A dermoscopic photograph of a skin lesion:
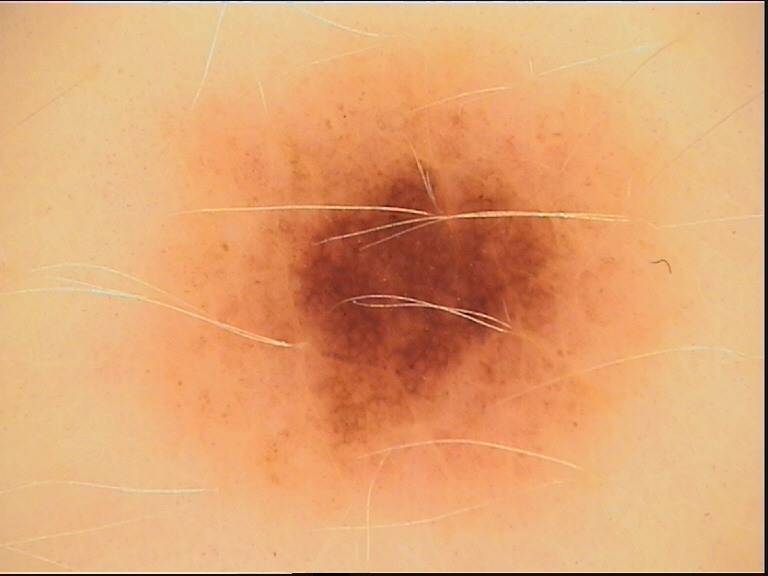Consistent with a benign lesion — a dysplastic compound nevus.